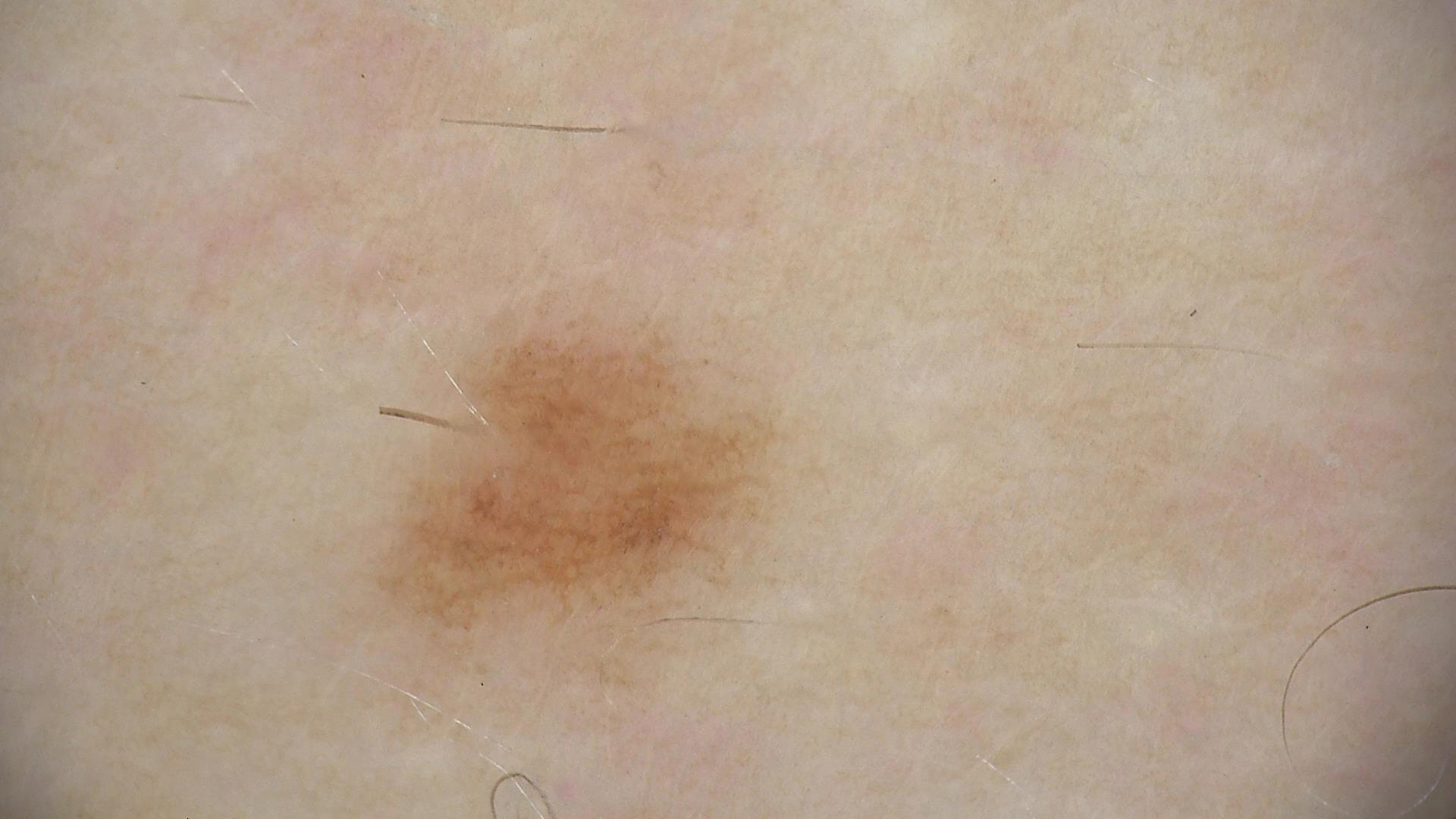Diagnosed as a banal lesion — a junctional nevus.